The lesion involves the arm. Texture is reported as raised or bumpy. The condition has been present for less than one week. The patient described the issue as a rash. The contributor is a male aged 40–49. Close-up view: 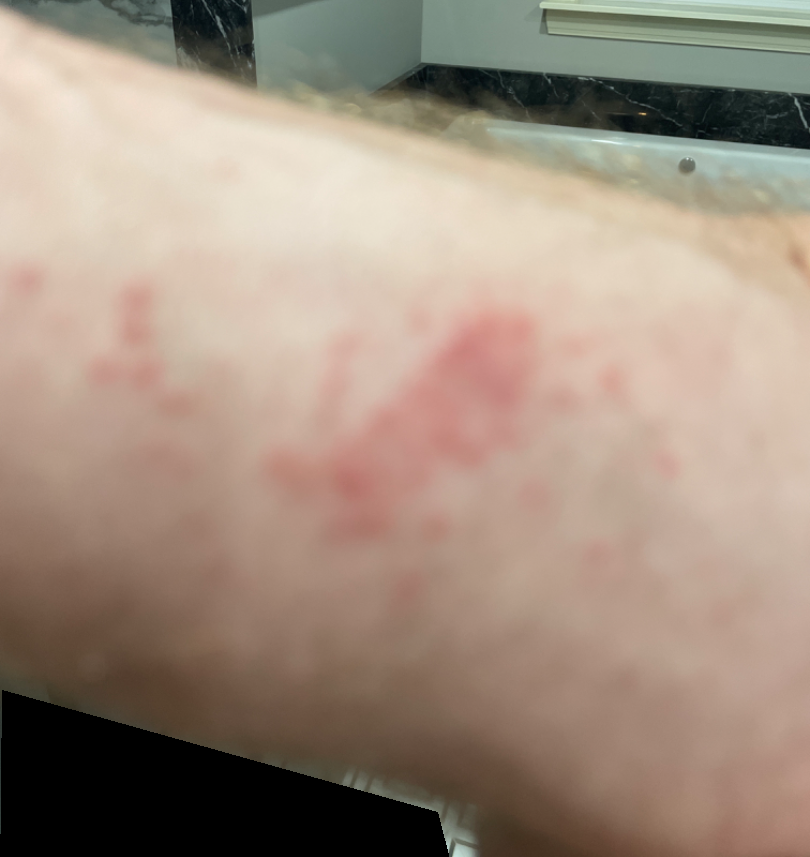{"assessment": "indeterminate from the photograph"}